The arm is involved; the photo was captured at a distance; the condition has been present for one to three months: 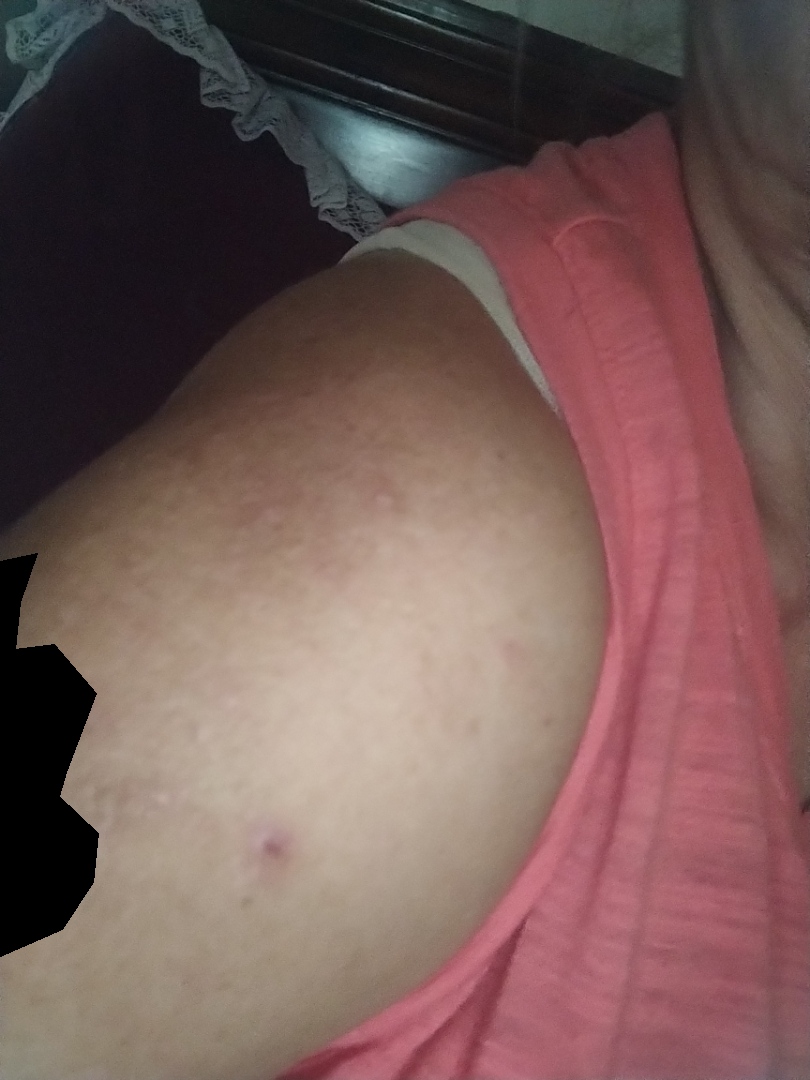Findings: On remote review of the image: the favored diagnosis is Folliculitis.